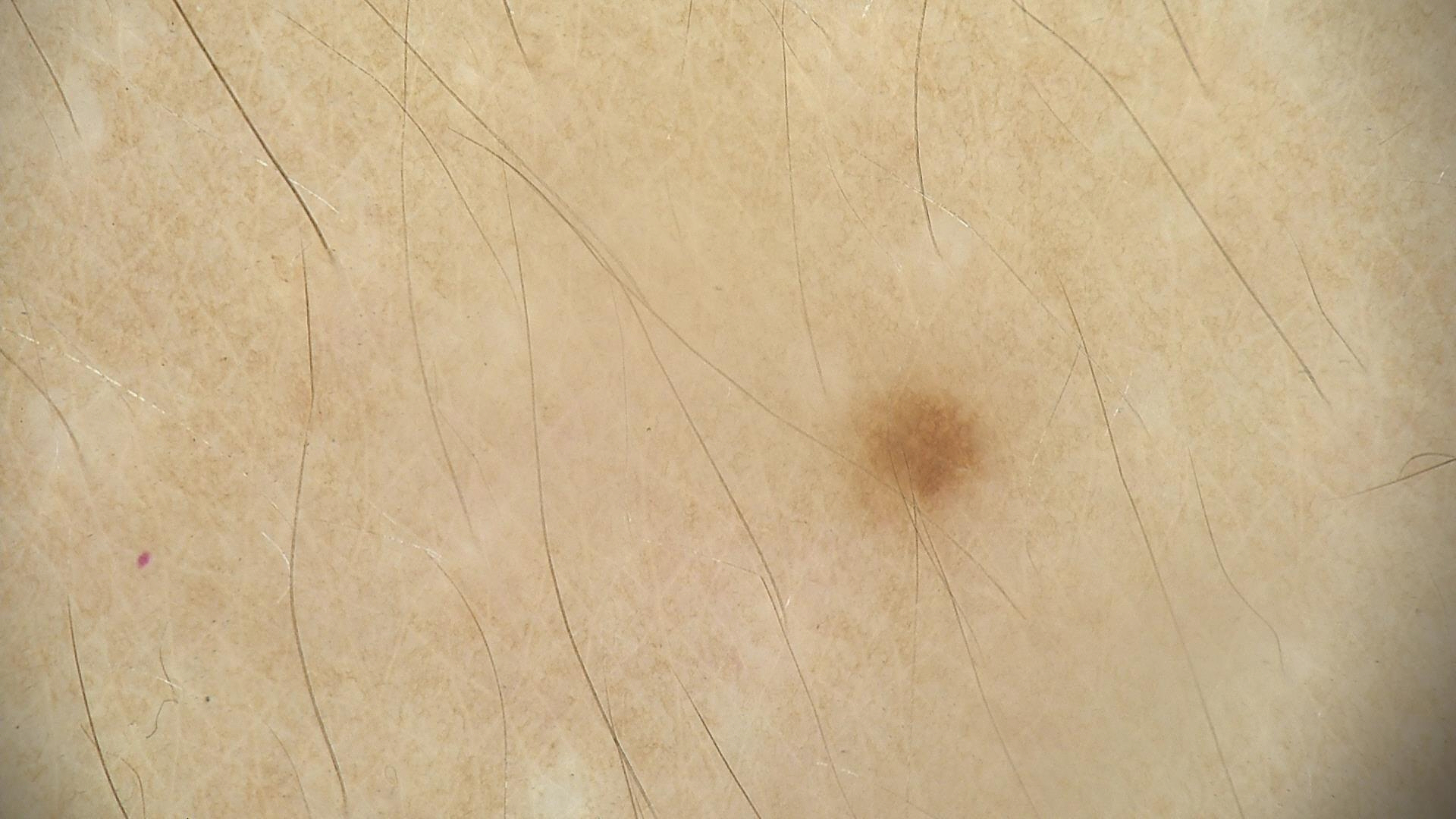Q: What is the imaging modality?
A: dermoscopy
Q: What is this lesion?
A: dysplastic junctional nevus (expert consensus)